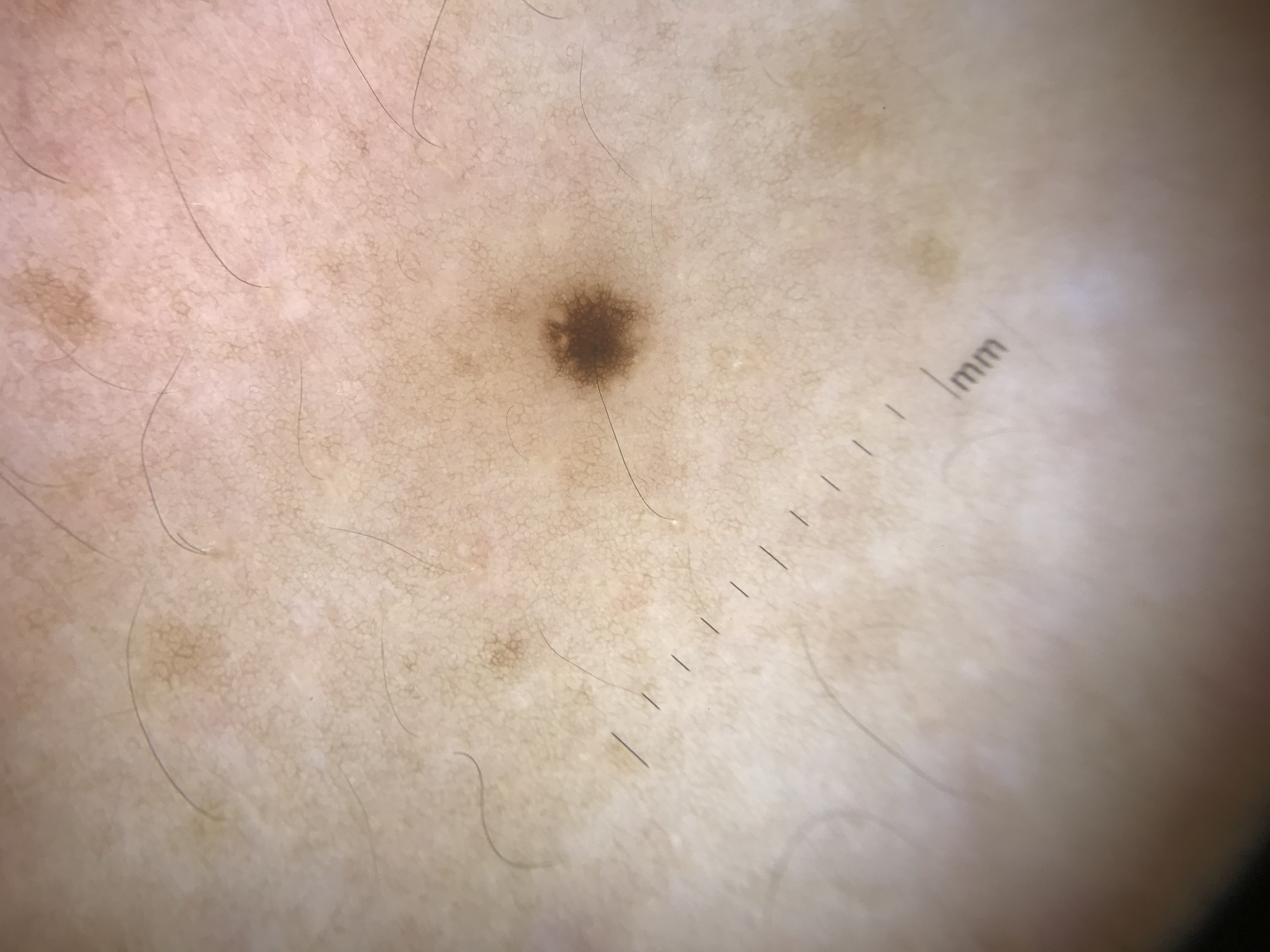Classified as a junctional nevus.